Imaged for a research study, with no referral diagnosis recorded; the patient says their skin reddens with sun exposure; a male subject 66 years old.
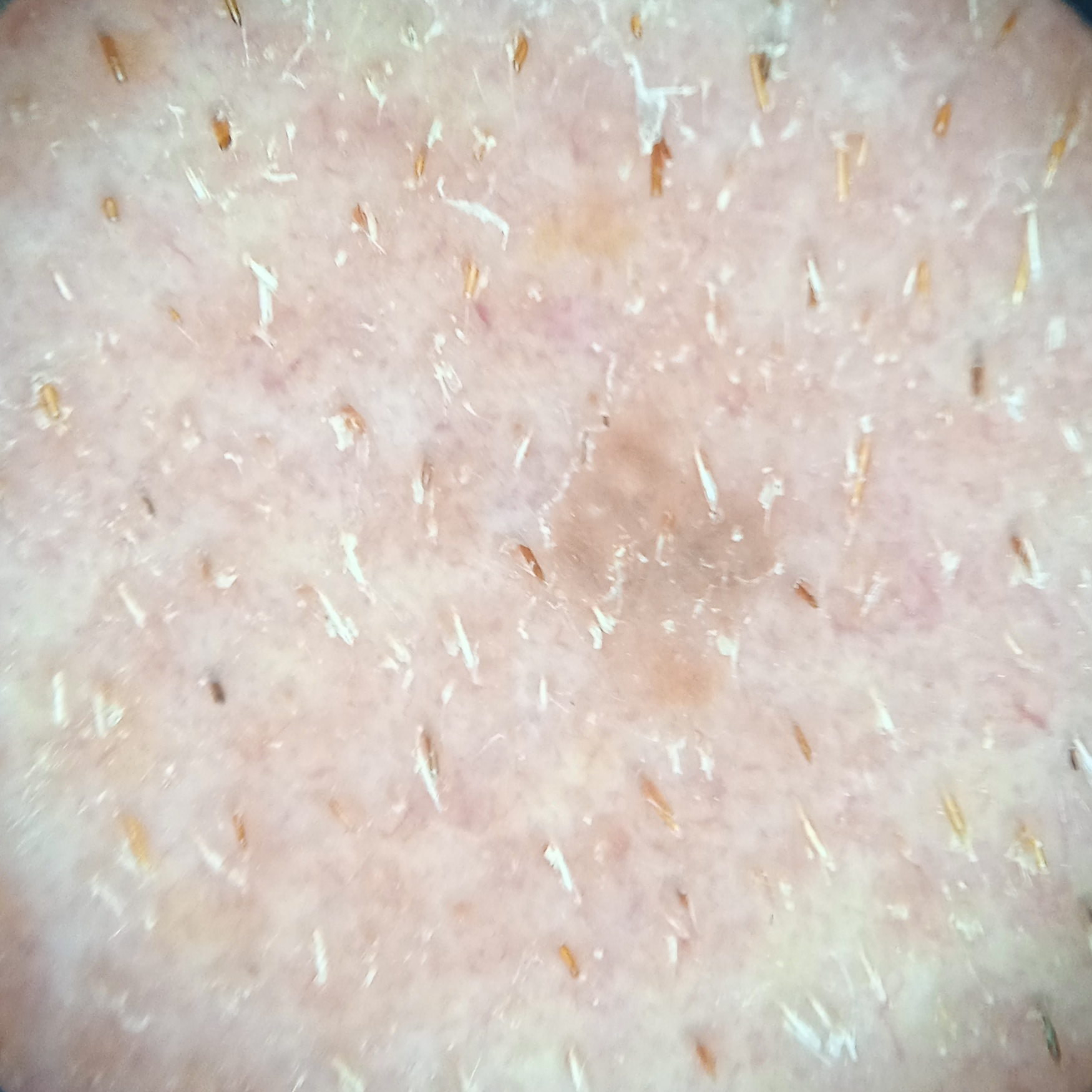The lesion measures approximately 3 mm.
Dermatologist review favored a seborrheic keratosis.